The photograph was taken at an angle — 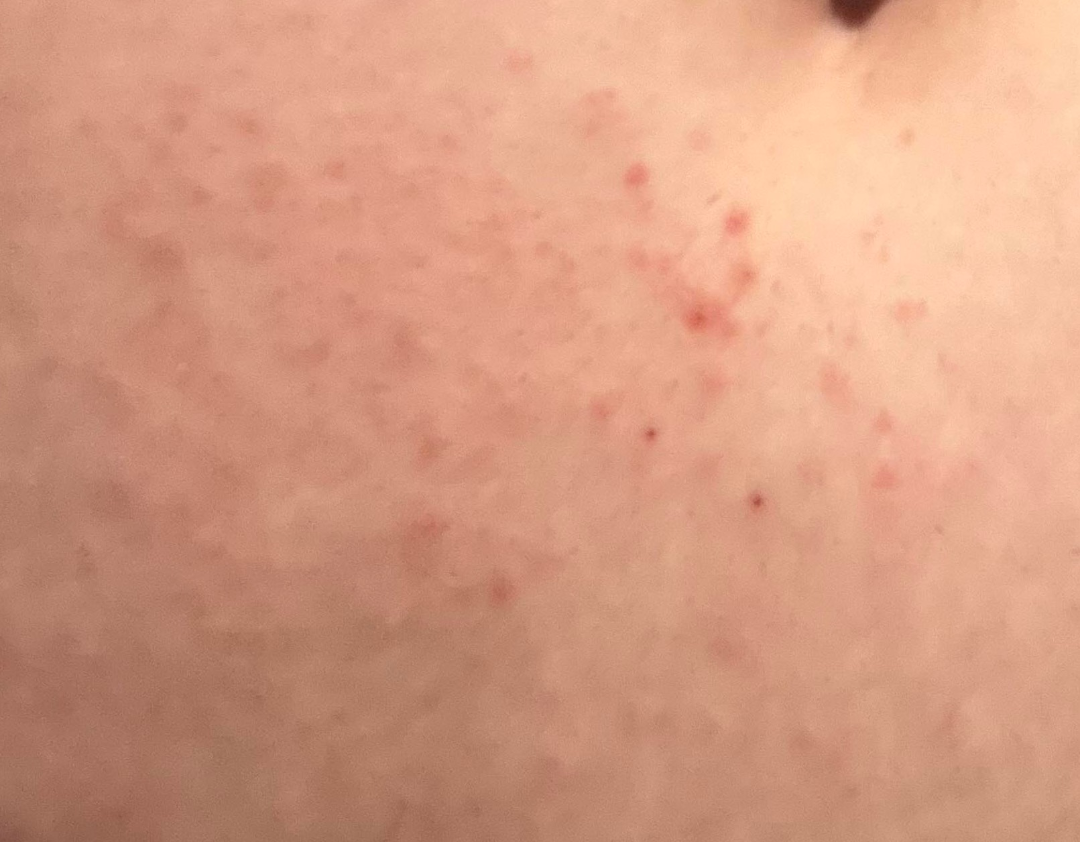impression = Eczema (most likely); Pemphigoid gestationis (possible); Pruritic urticarial papules and plaques of pregnancy (possible).